The photograph is a close-up of the affected area · the lesion is described as flat · reported duration is less than one week · located on the back of the torso, top or side of the foot, front of the torso, leg and head or neck — 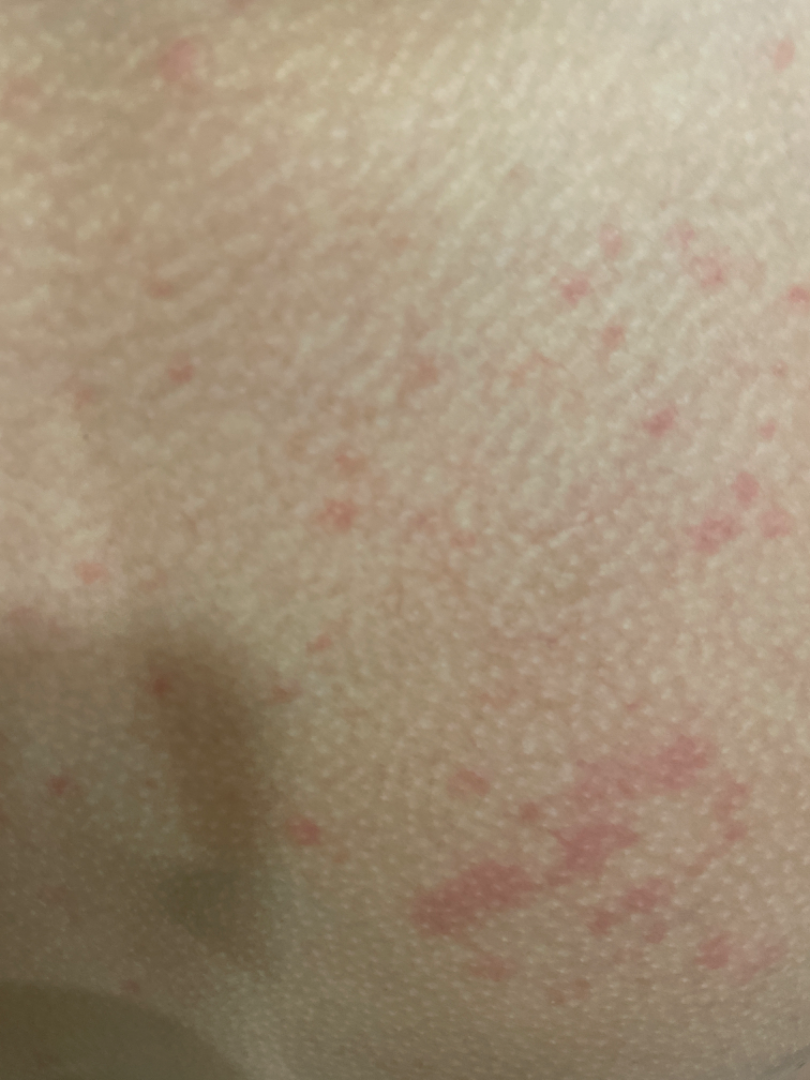Notes:
- diagnostic considerations — Eczema (0.33); Hypersensitivity (0.33); Allergic Contact Dermatitis (0.33)